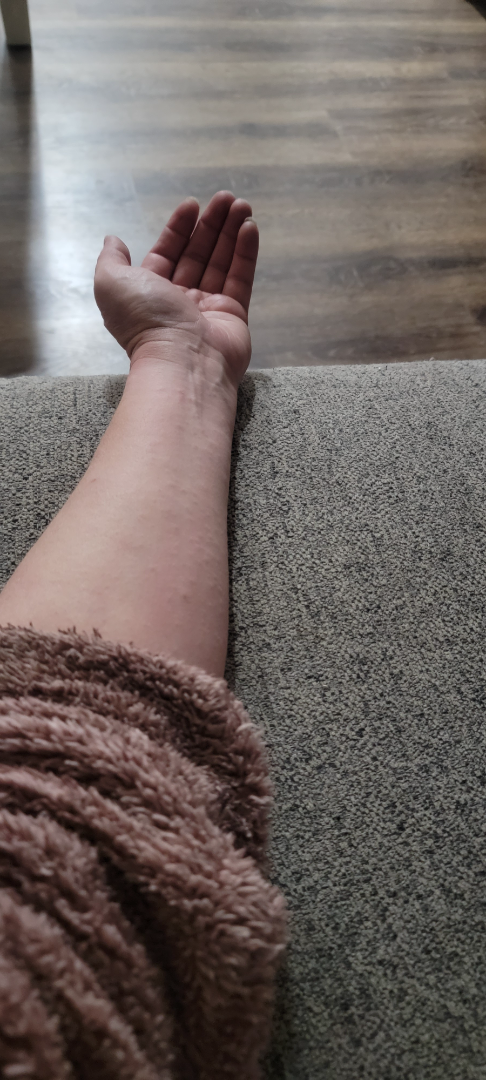<dermatology_case>
<body_site>arm, leg</body_site>
<duration>less than one week</duration>
<skin_tone>
  <fitzpatrick>III</fitzpatrick>
</skin_tone>
<patient_category>a rash</patient_category>
<texture>raised or bumpy</texture>
<shot_type>at a distance</shot_type>
<patient>female, age 40–49</patient>
<symptoms>itching, burning</symptoms>
<differential>
  <leading>Allergic Contact Dermatitis</leading>
  <considered>Lichenoid myxedema</considered>
  <unlikely>Viral Exanthem</unlikely>
</differential>
</dermatology_case>